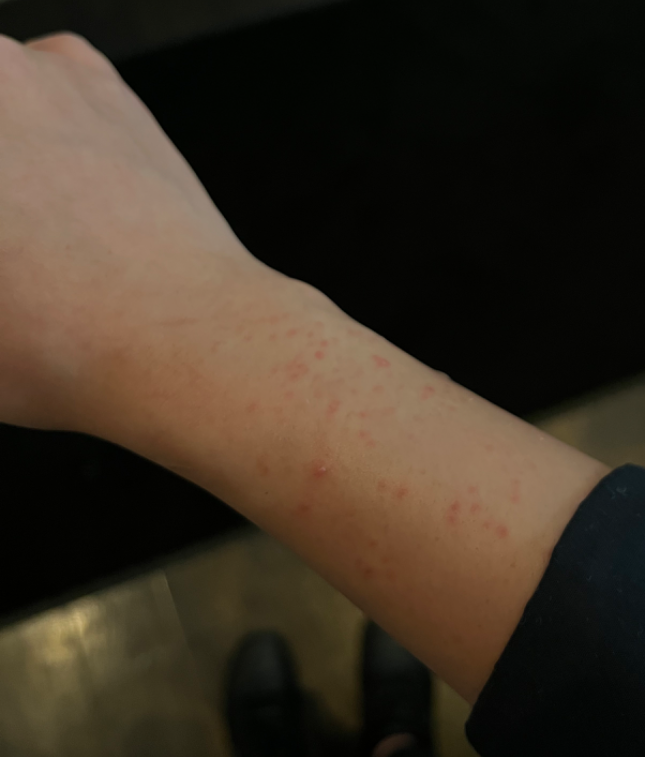| feature | finding |
|---|---|
| image framing | close-up |
| body site | arm |
| differential diagnosis | the primary impression is Folliculitis; possibly Insect Bite; an alternative is Irritant Contact Dermatitis |